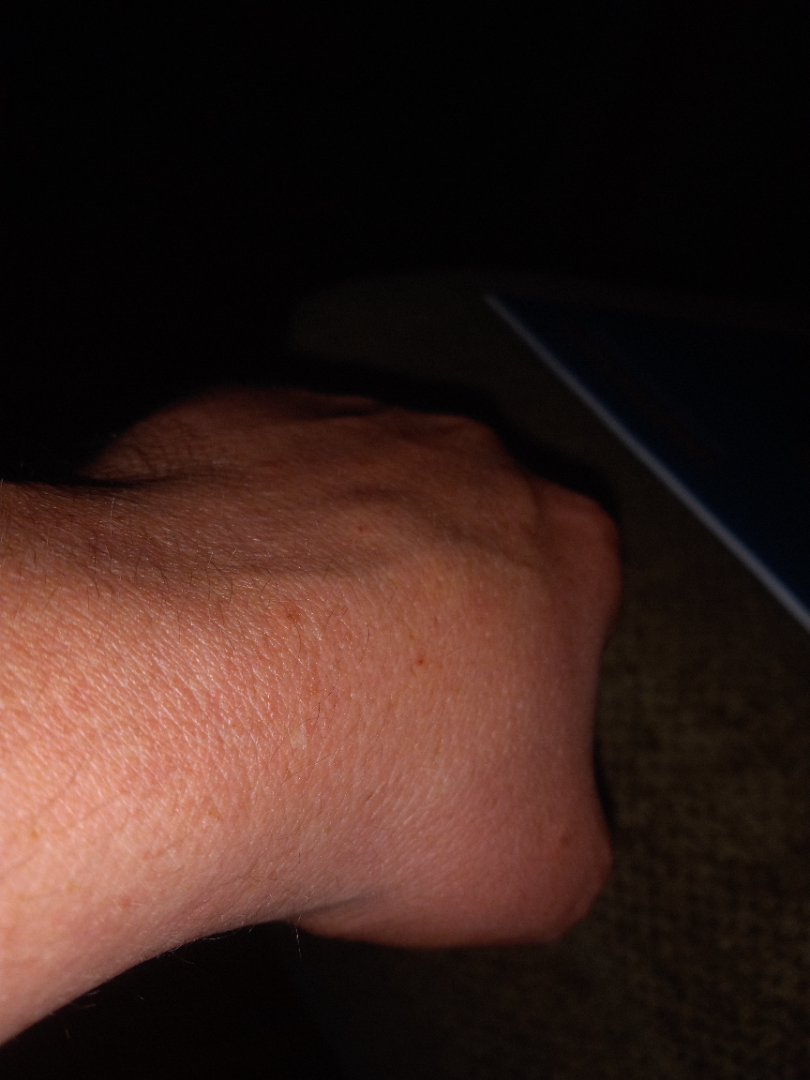Notes:
- assessment: indeterminate from the photograph
- view: at an angle
- body site: arm, sole of the foot, back of the hand, top or side of the foot and leg